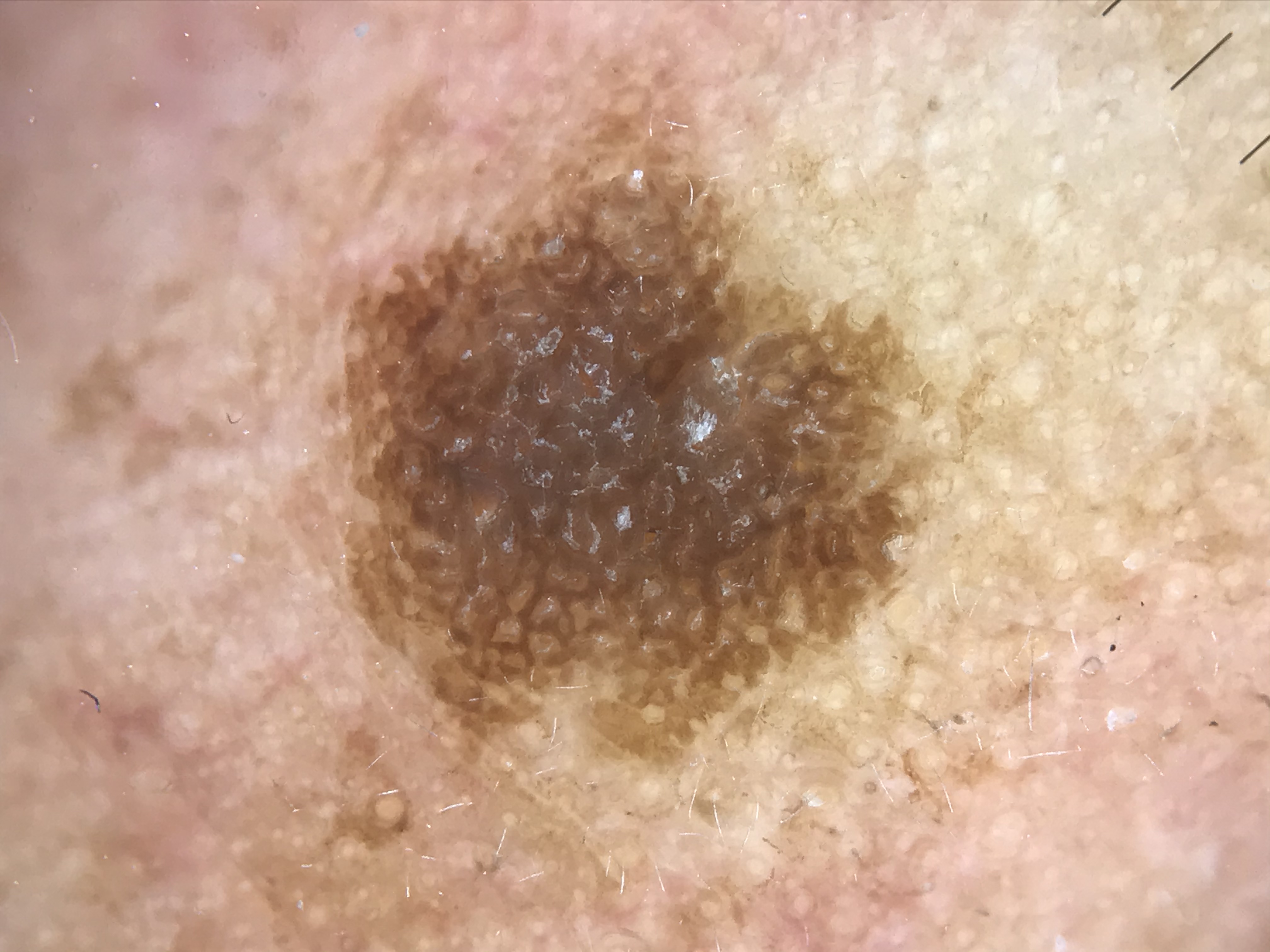Case:
A dermoscopic close-up of a skin lesion. This is a keratinocytic lesion.
Conclusion:
Classified as a seborrheic keratosis.